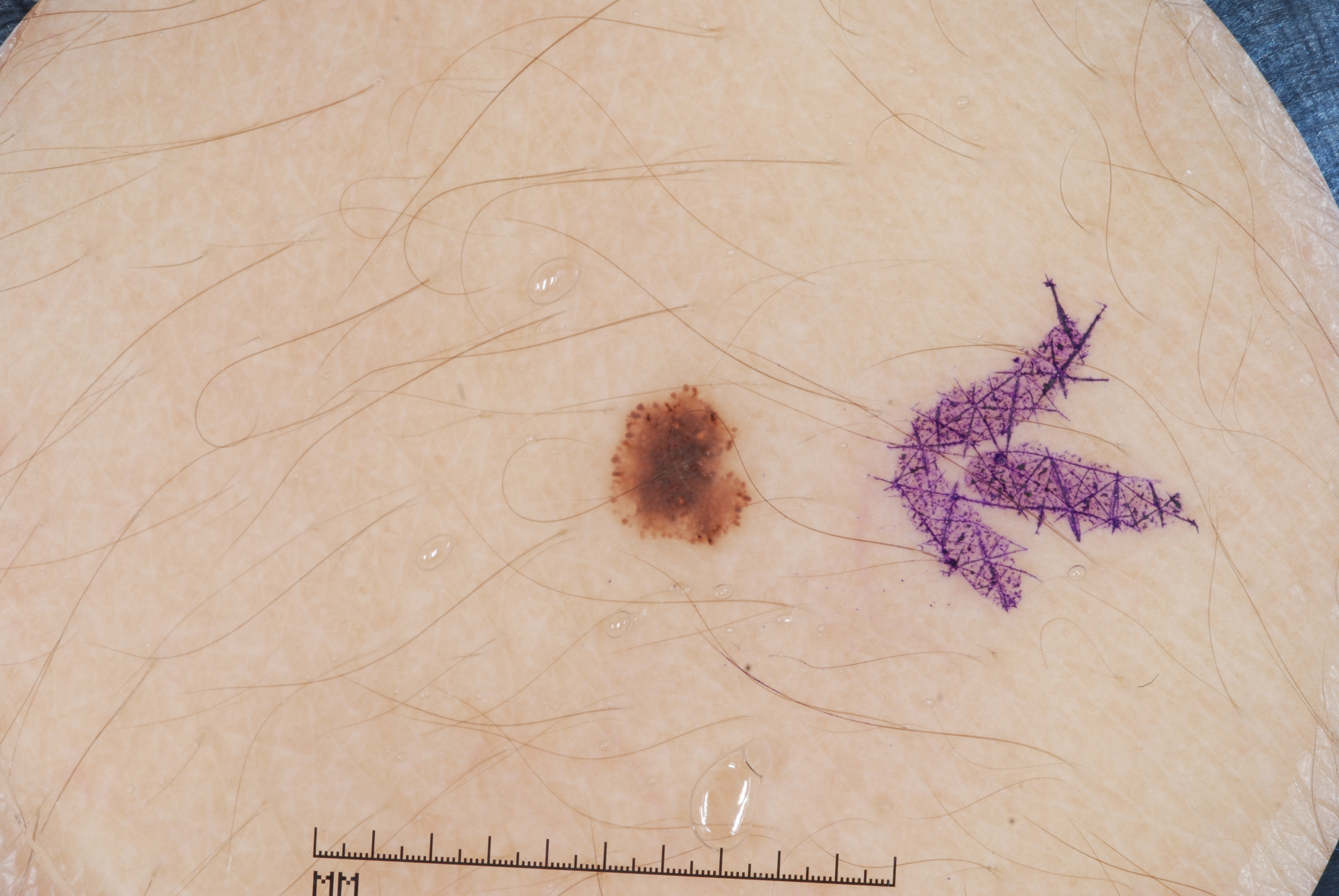| key | value |
|---|---|
| modality | dermatoscopic image of a skin lesion |
| patient | male, aged approximately 25 |
| features | streaks; absent: milia-like cysts, pigment network, and negative network |
| extent | ~1% of the field |
| lesion location | (617, 393, 742, 539) |
| diagnostic label | a melanocytic nevus |